A dermoscopy image of a single skin lesion: 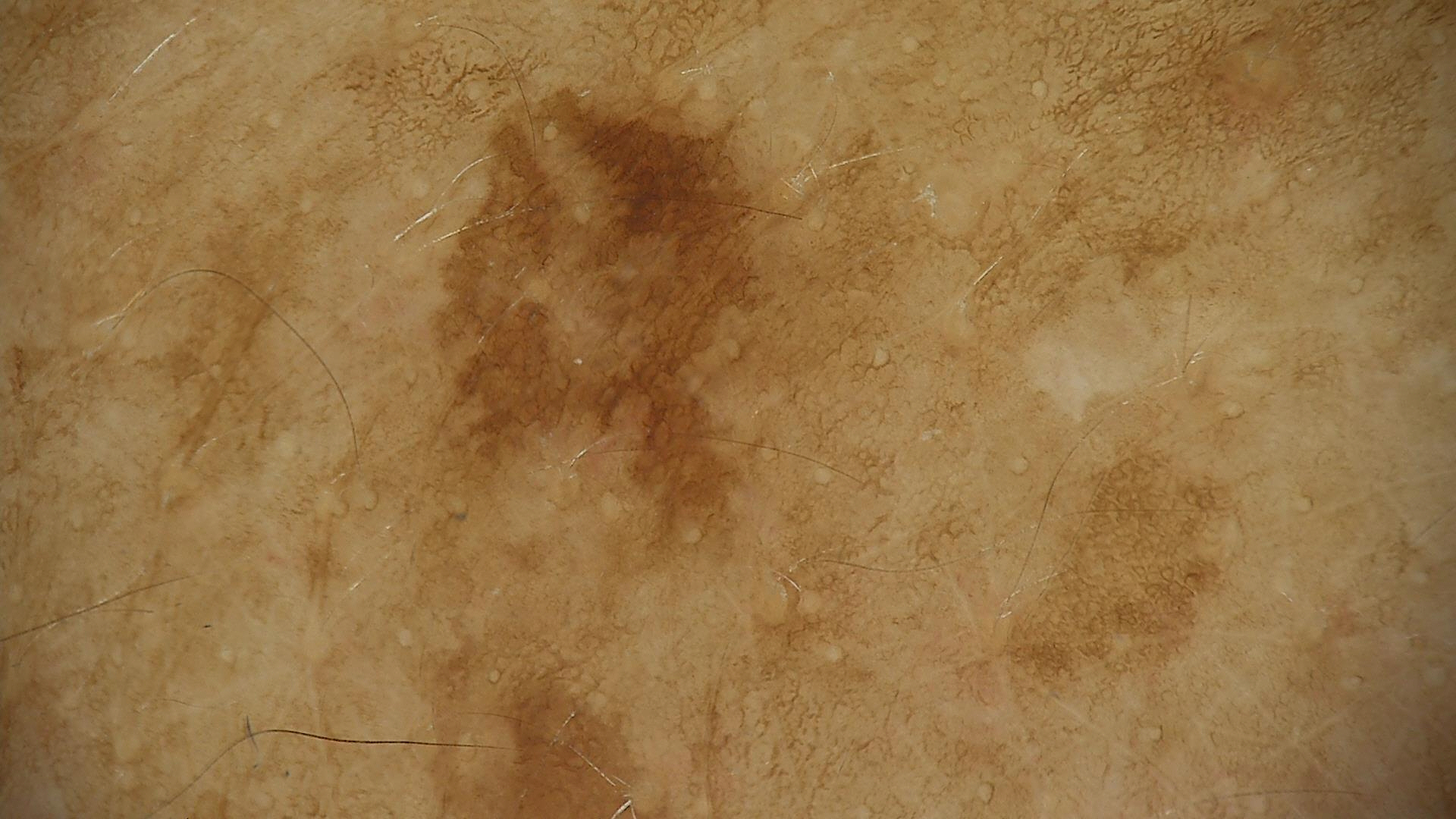The diagnosis was a solar lentigo.